A dermoscopy image of a single skin lesion.
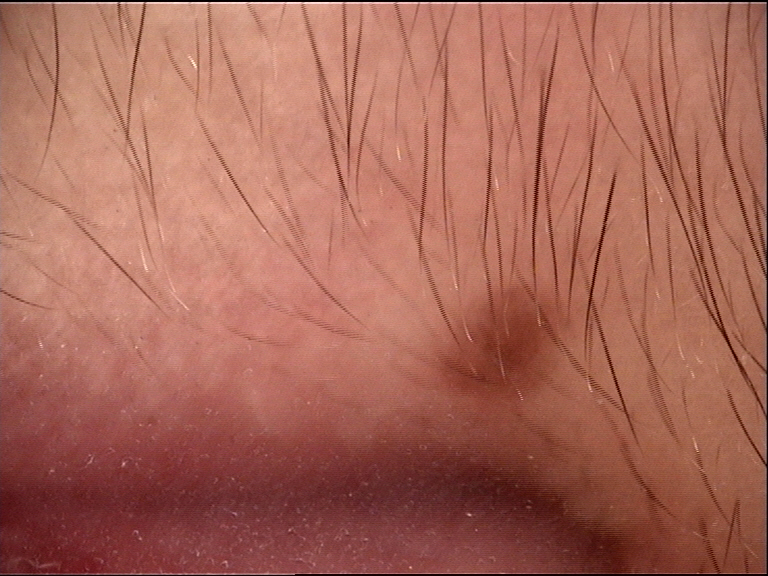subtype: banal, compound | class: Miescher nevus (expert consensus).